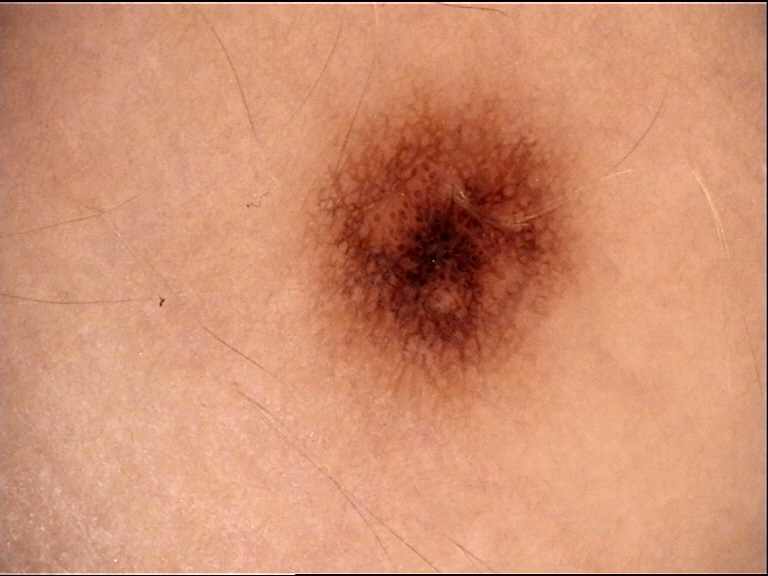Case:
- class · dysplastic junctional nevus (expert consensus)